A dermatoscopic image of a skin lesion.
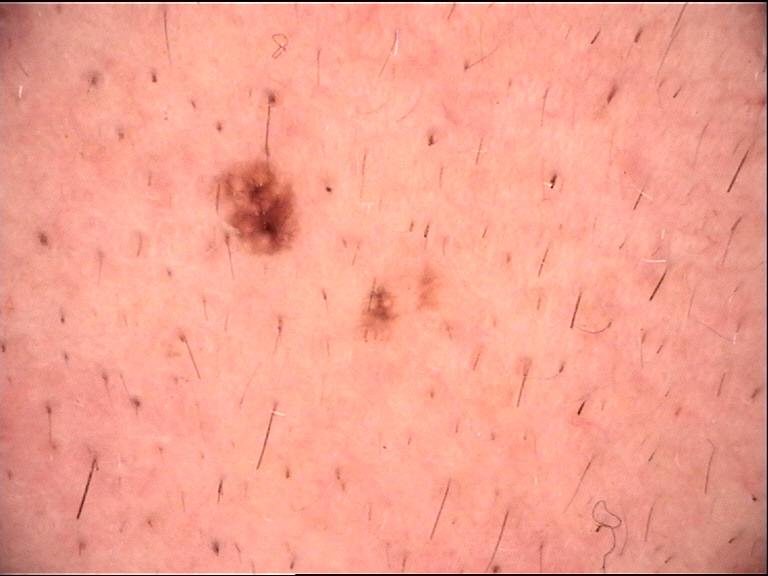assessment = Miescher nevus (expert consensus).